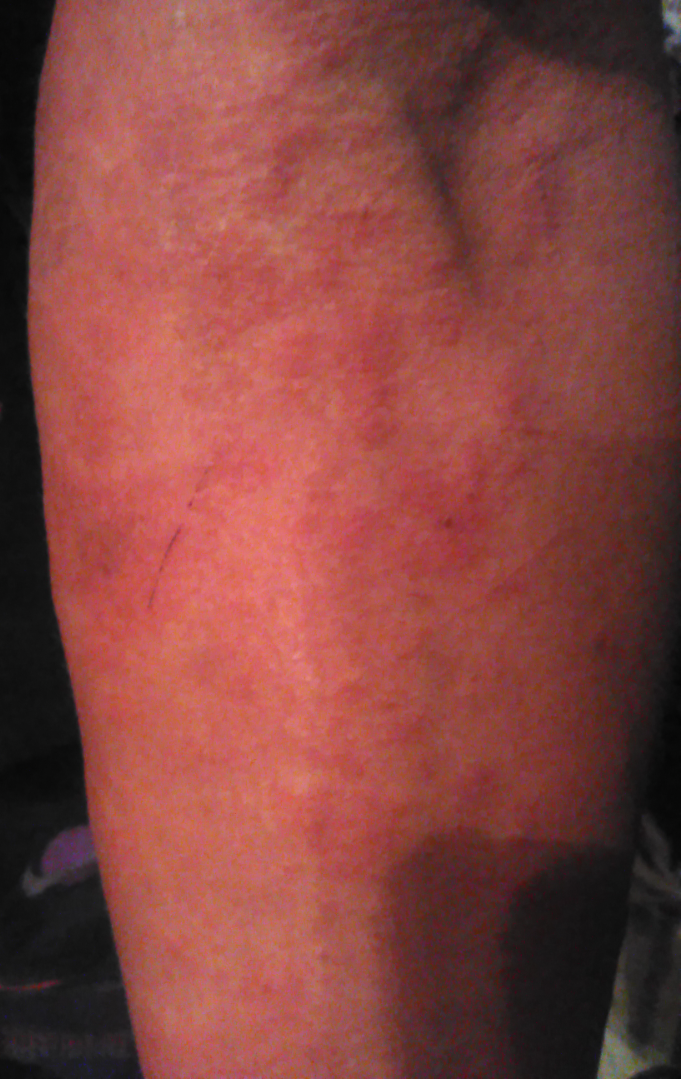photo taken = close-up | clinical impression = single-reviewer assessment: the differential, in no particular order, includes Hypersensitivity and Allergic Contact Dermatitis.